An image taken at a distance — 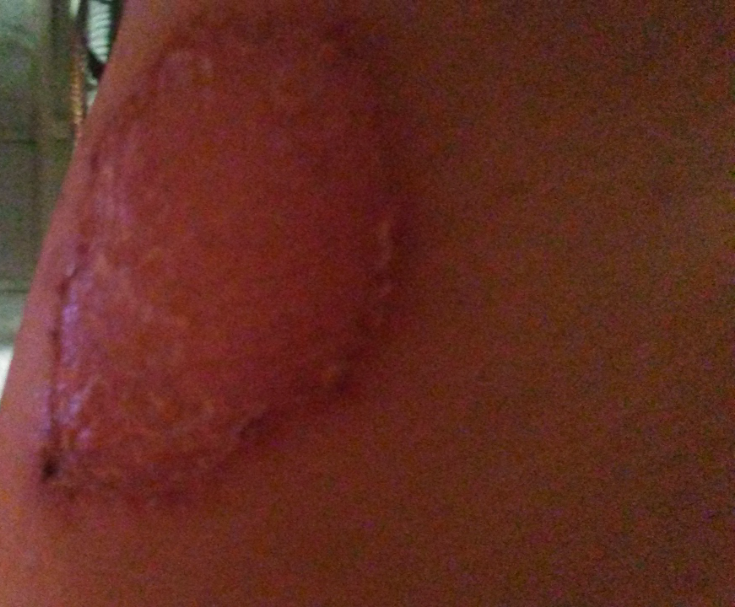Most consistent with Ecthyma; also on the differential is Porokeratosis; possibly Eczema.